A dermoscopic close-up of a skin lesion.
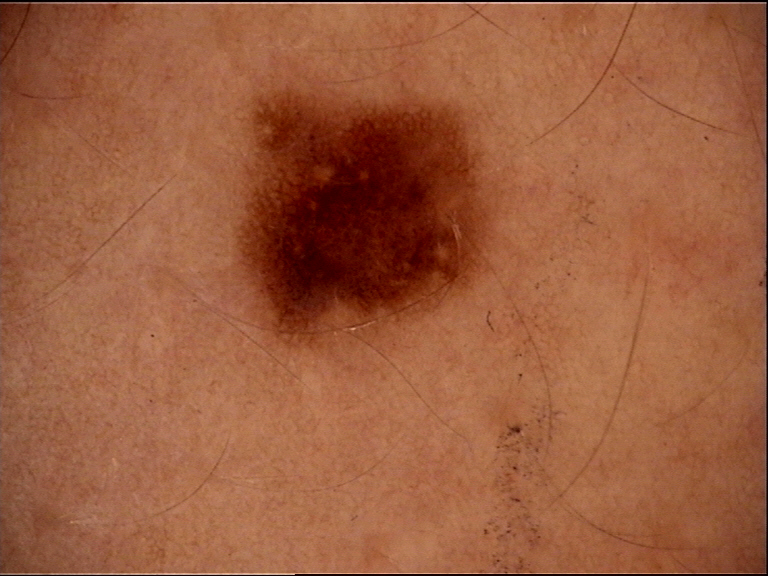Conclusion:
The diagnosis was a benign lesion — a dysplastic junctional nevus.